Recorded as Fitzpatrick phototype II. A clinical photograph of a skin lesion. A female subject in their mid-30s. History notes prior malignancy (patient or family), no tobacco use, and no pesticide exposure:
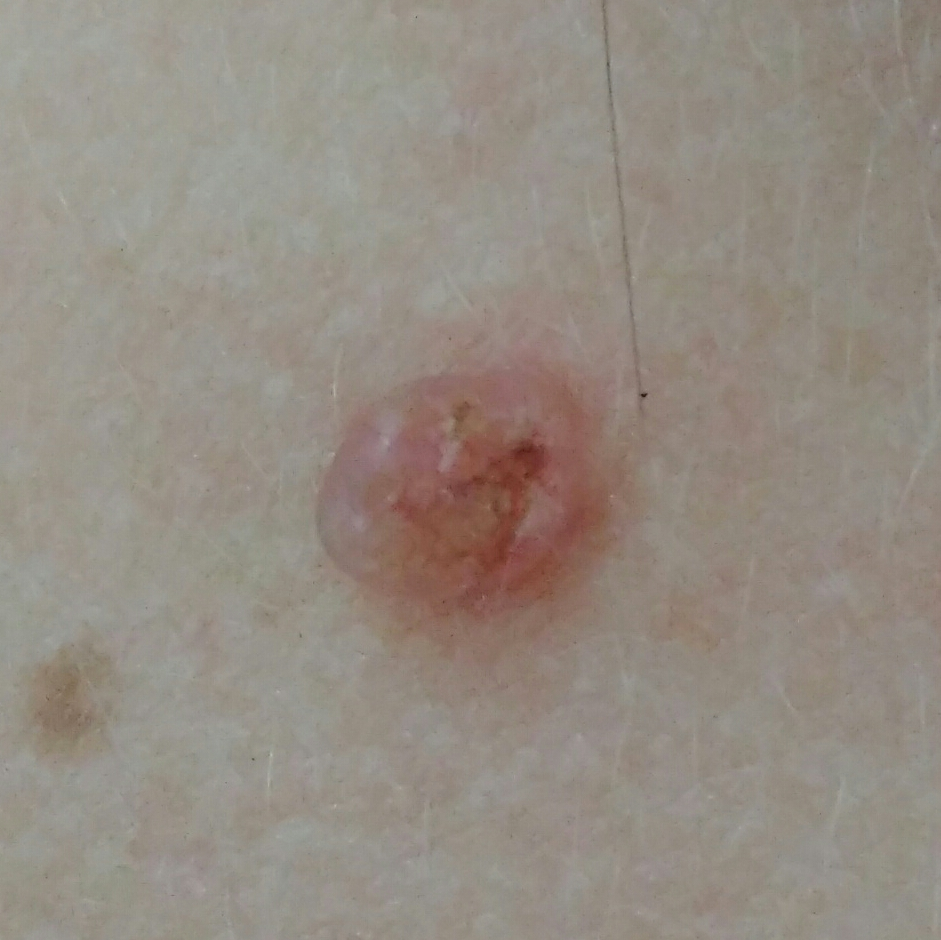Notes:
• region — the neck
• diameter — 5x5 mm
• patient-reported symptoms — bleeding, itching, elevation, pain, growth
• diagnostic label — basal cell carcinoma (biopsy-proven)